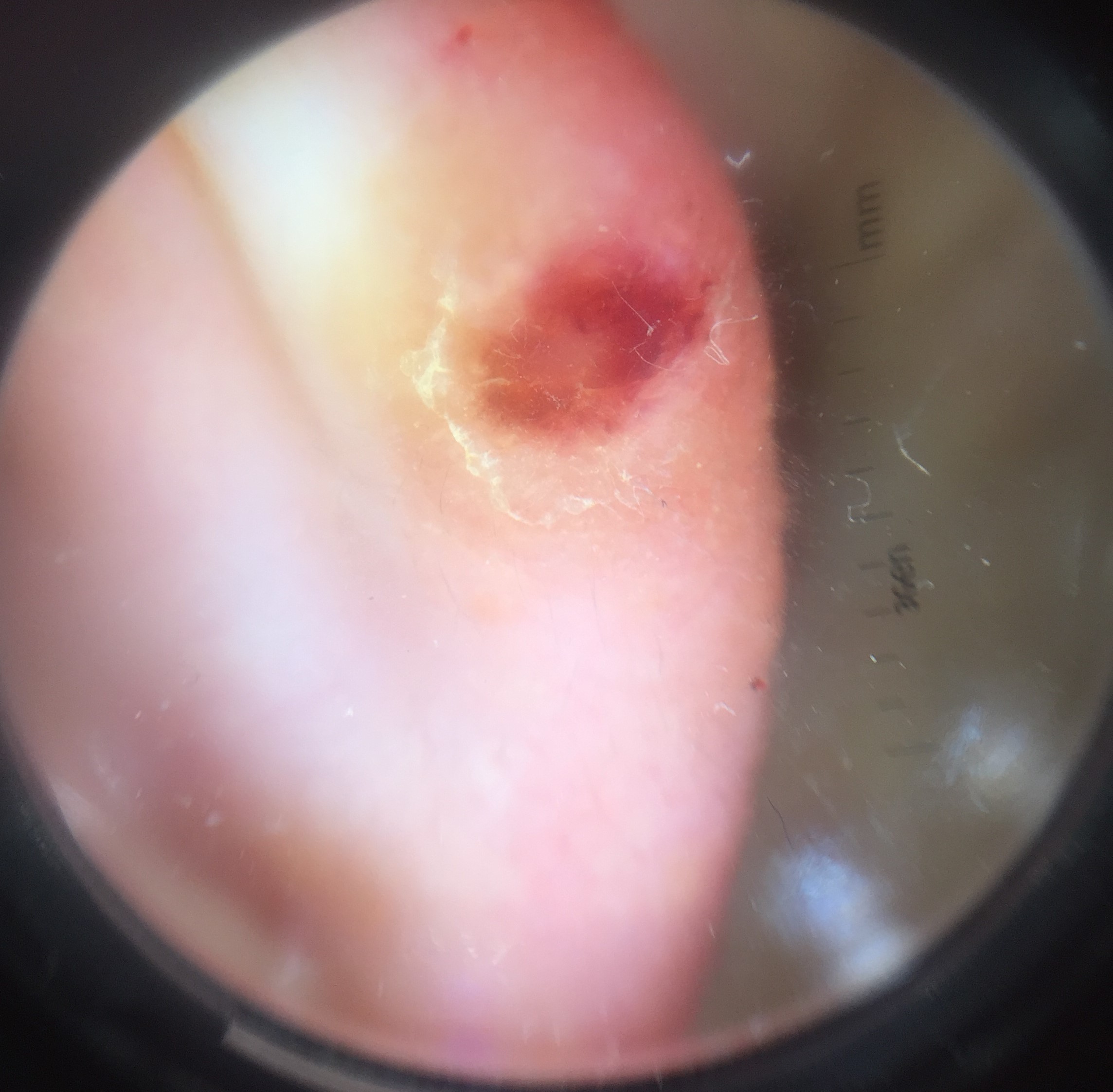imaging: dermoscopy
label: squamous cell carcinoma (biopsy-proven)